Close-up view — 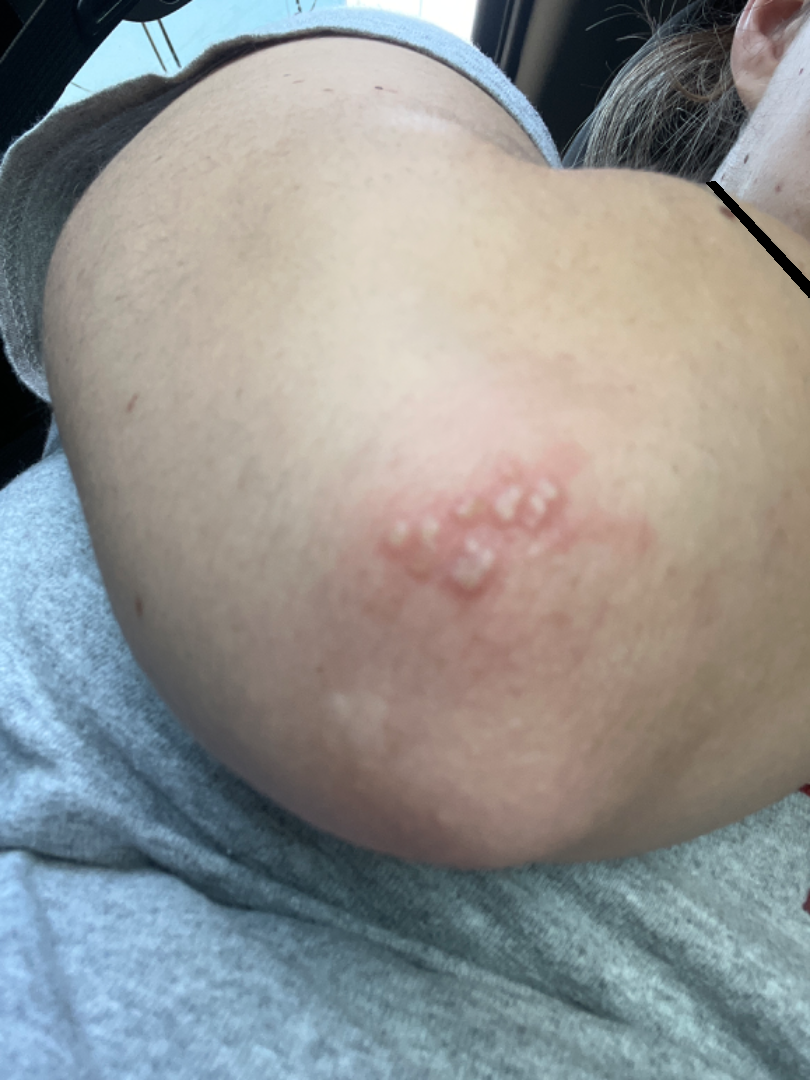| key | value |
|---|---|
| symptom duration | less than one week |
| constitutional symptoms | fatigue and fever |
| reported symptoms | itching, pain, enlargement and burning |
| described texture | raised or bumpy and fluid-filled |
| self-categorized as | skin that appeared healthy to them |
| assessment | the favored diagnosis is Herpes Simplex; with consideration of Impetigo; also on the differential is Herpes Zoster |